Imaged for a research study, with no referral diagnosis recorded. A dermoscopic image of a skin lesion. The patient describes having few moles overall:
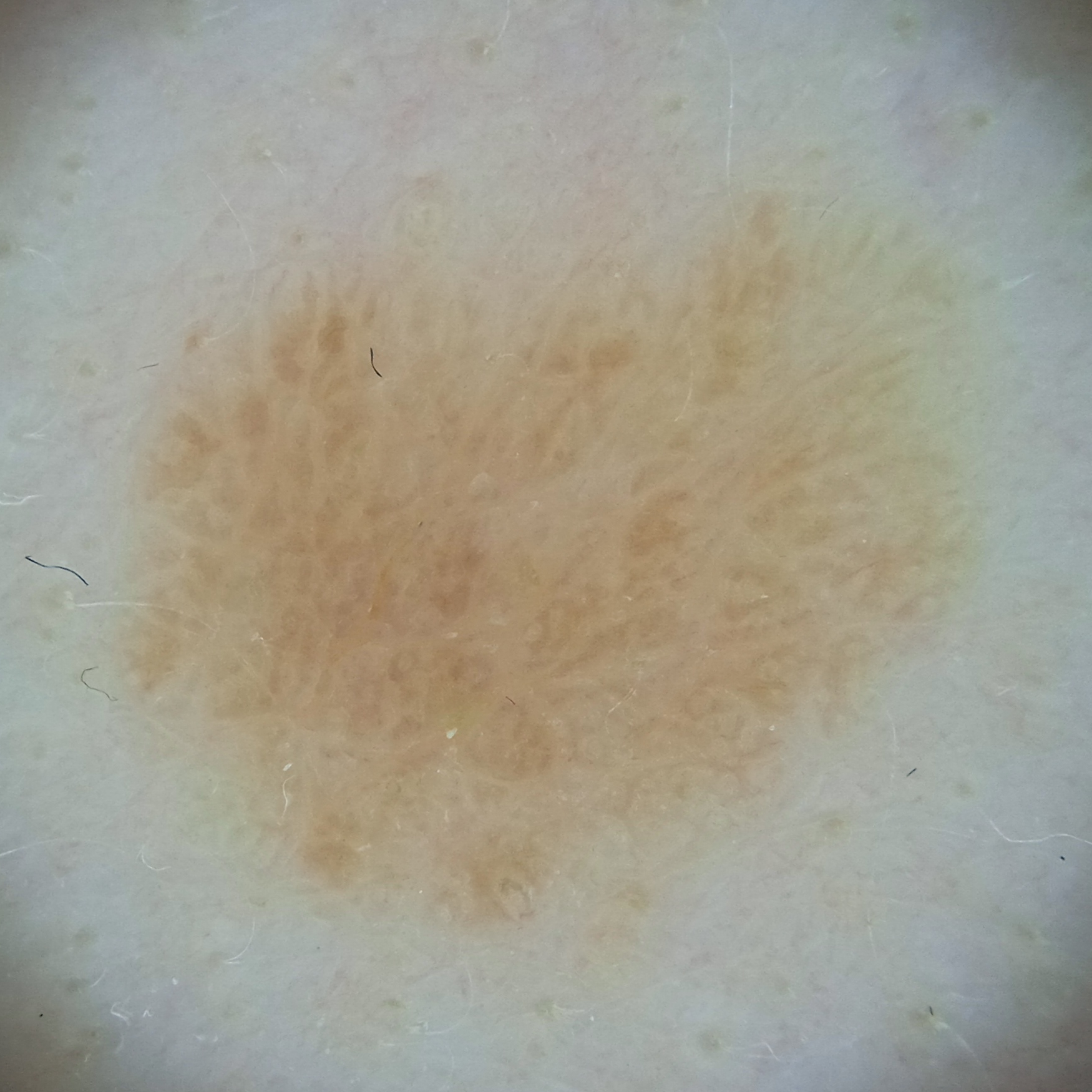Conclusion:
The lesion was assessed as a seborrheic keratosis.